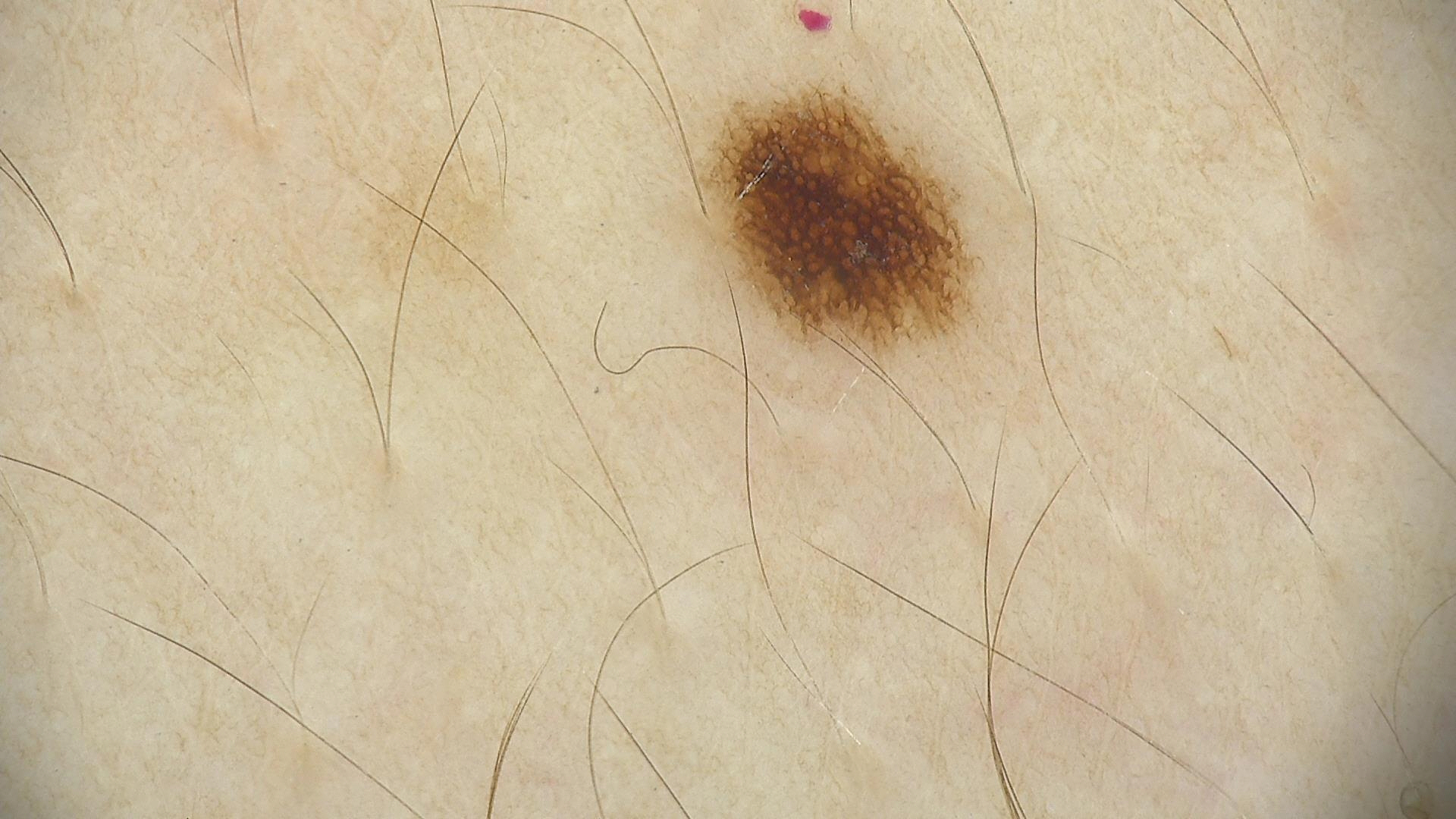diagnosis:
  name: dysplastic junctional nevus
  code: jd
  malignancy: benign
  super_class: melanocytic
  confirmation: expert consensus